Contact-polarized dermoscopy of a skin lesion · a male patient aged 83 or older: 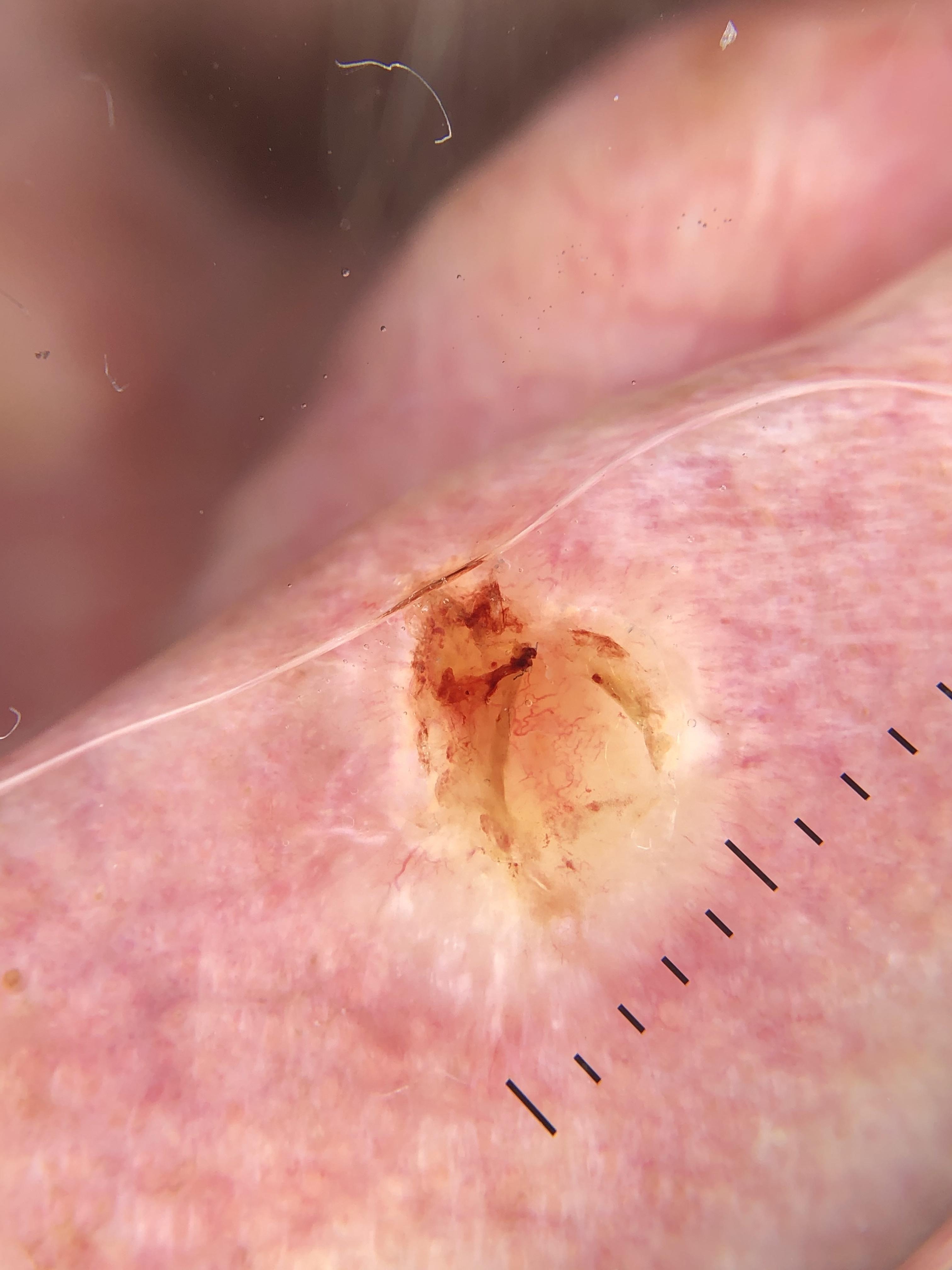{
  "lesion_location": {
    "region": "the head or neck"
  },
  "diagnosis": {
    "name": "Basal cell carcinoma",
    "malignancy": "malignant",
    "confirmation": "histopathology",
    "lineage": "adnexal"
  }
}